This is a dermoscopic photograph of a skin lesion. A male patient, approximately 70 years of age — 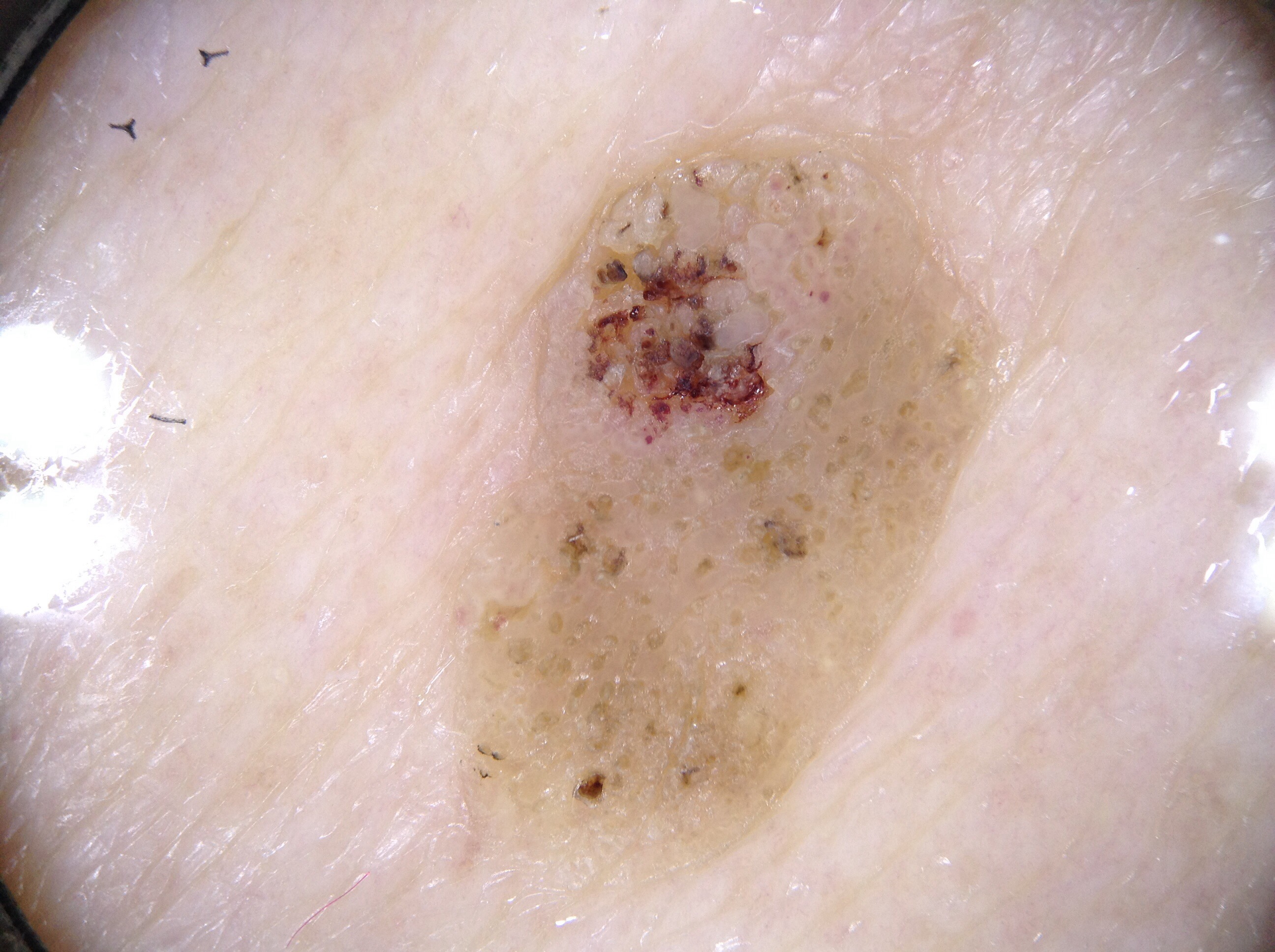- lesion bbox · 451, 102, 1006, 873
- lesion size · moderate
- dermoscopic features assessed but absent · negative network, pigment network, milia-like cysts, and streaks
- impression · a seborrheic keratosis, a keratinocytic lesion